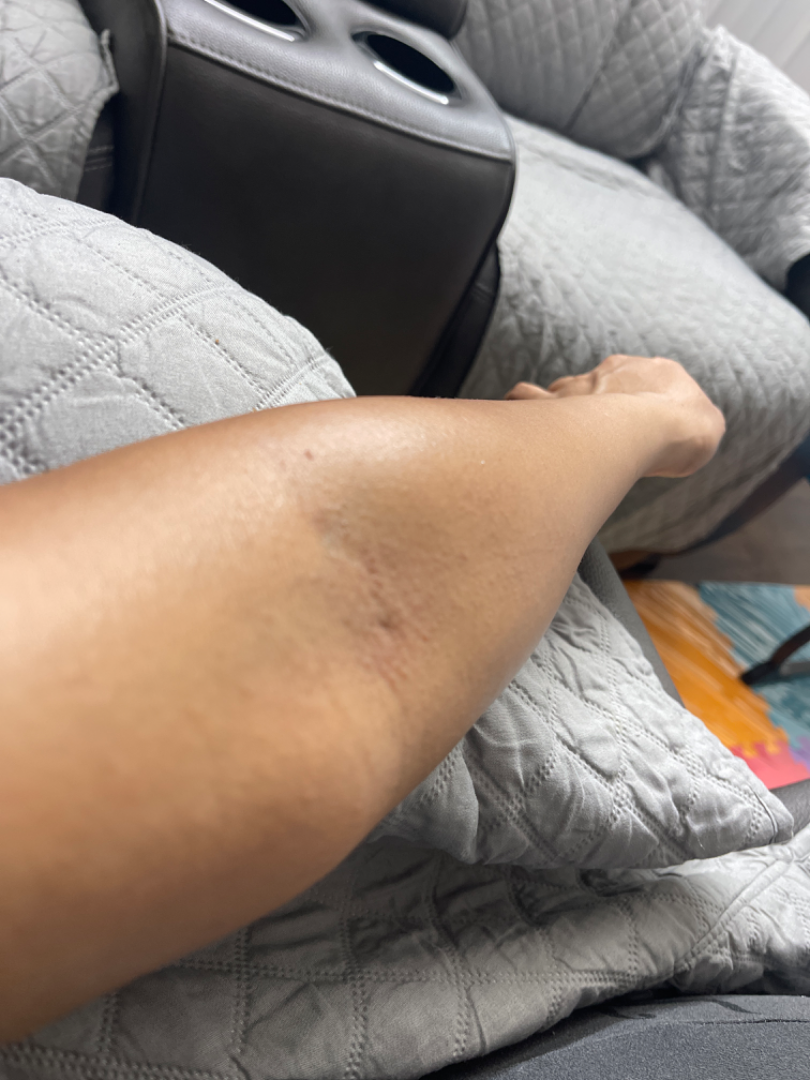An image taken at an angle.
Reported lesion symptoms include burning and itching.
The arm is involved.
The reviewer's impression was Eczema.